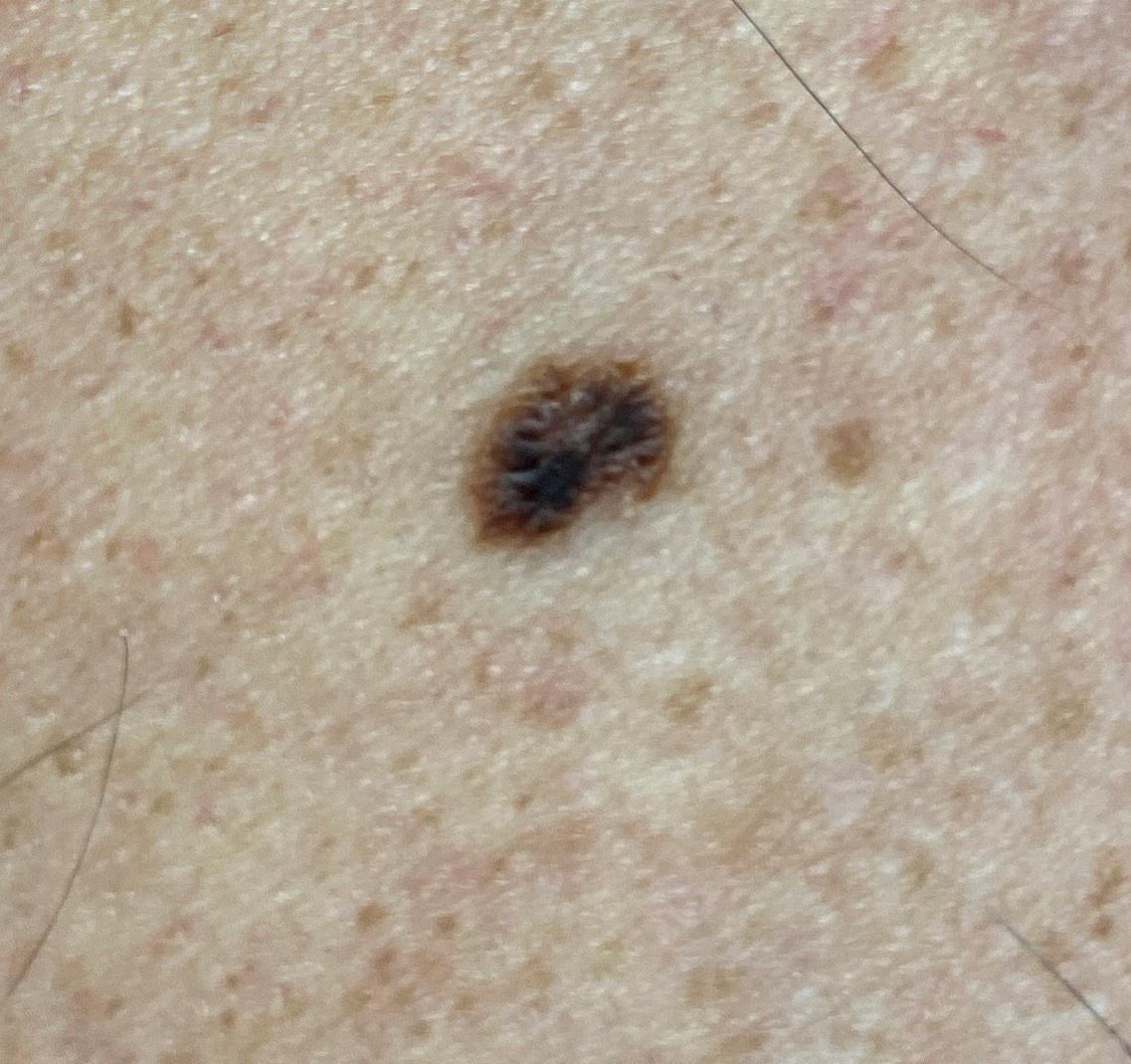A male subject aged around 50.
A wide-field clinical photograph of a skin lesion.
Located on the anterior trunk.
On biopsy, the diagnosis was a nevus.